A dermoscopy image of a single skin lesion.
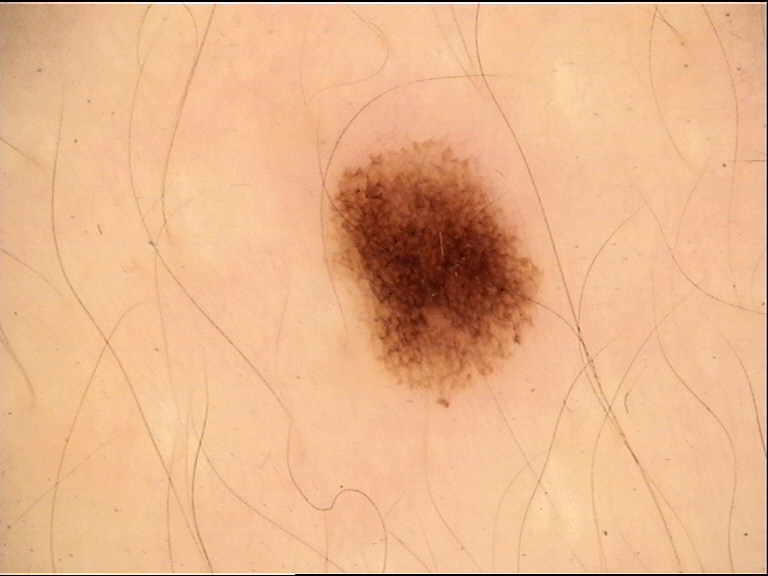The diagnostic label was a dysplastic junctional nevus.